A female patient aged 20 · acquired for a research image collection, with no referral diagnosis · on a questionnaire the patient reported no personal history of cancer and no personal history of skin cancer · the patient says their skin reddens with sun exposure · the patient describes having a moderate number of moles · a clinical photograph showing a skin lesion.
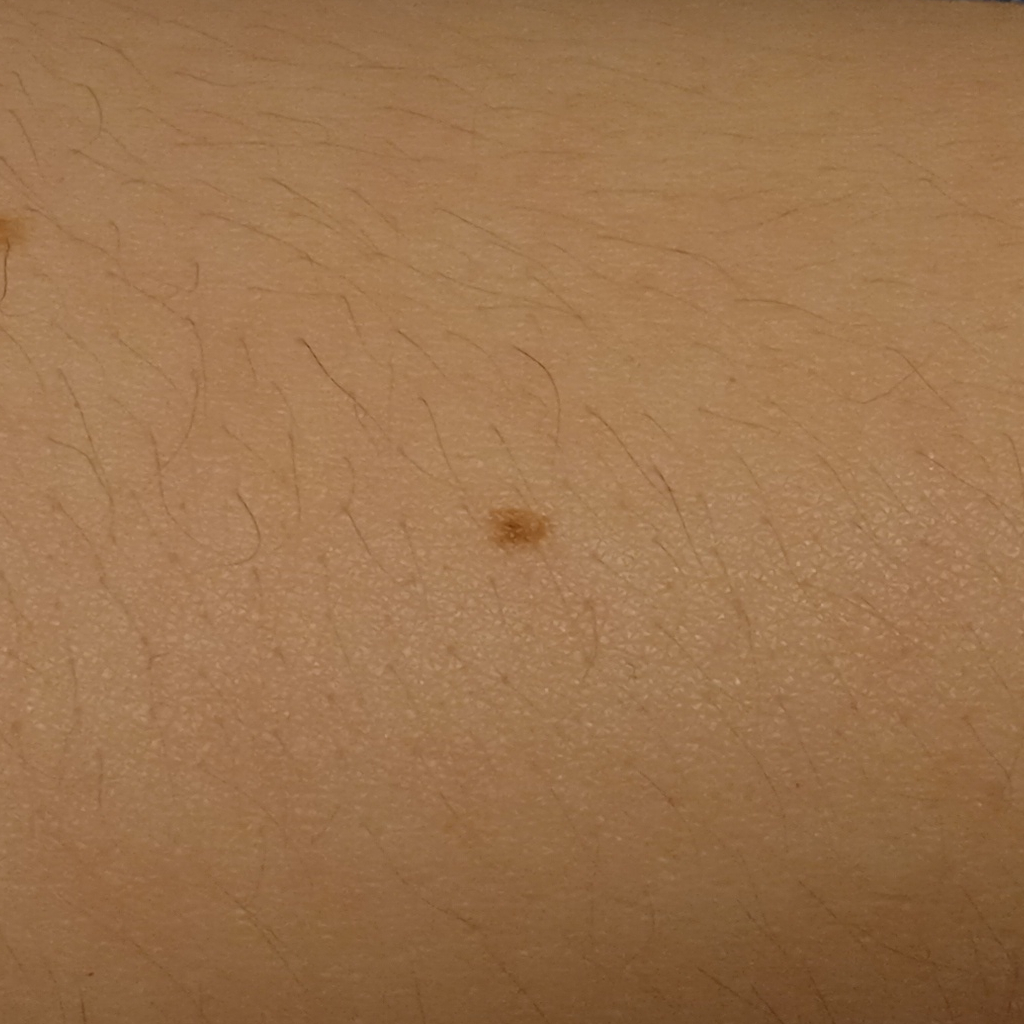Summary: The lesion is located on an arm. The lesion is about 2.5 mm across. Conclusion: The dermatologists' assessment was a melanocytic nevus.